A dermoscopy image of a single skin lesion.
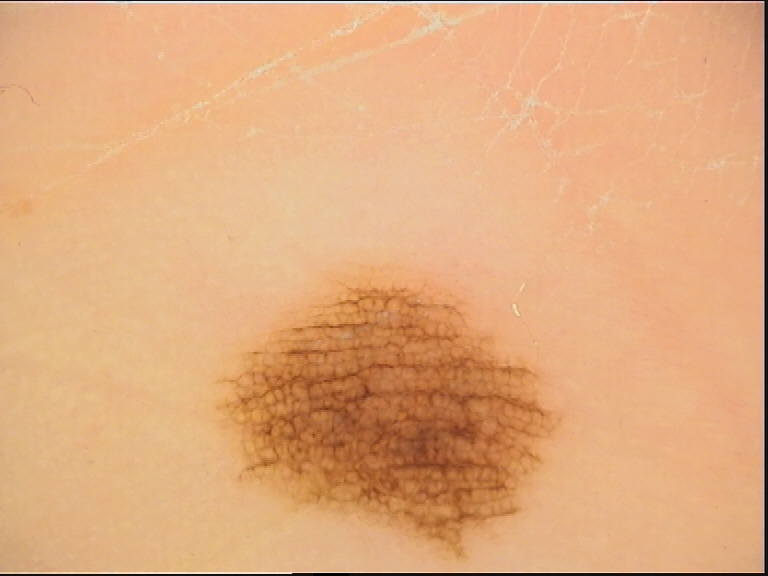Labeled as a benign lesion — an acral dysplastic junctional nevus.